This is a close-up image — 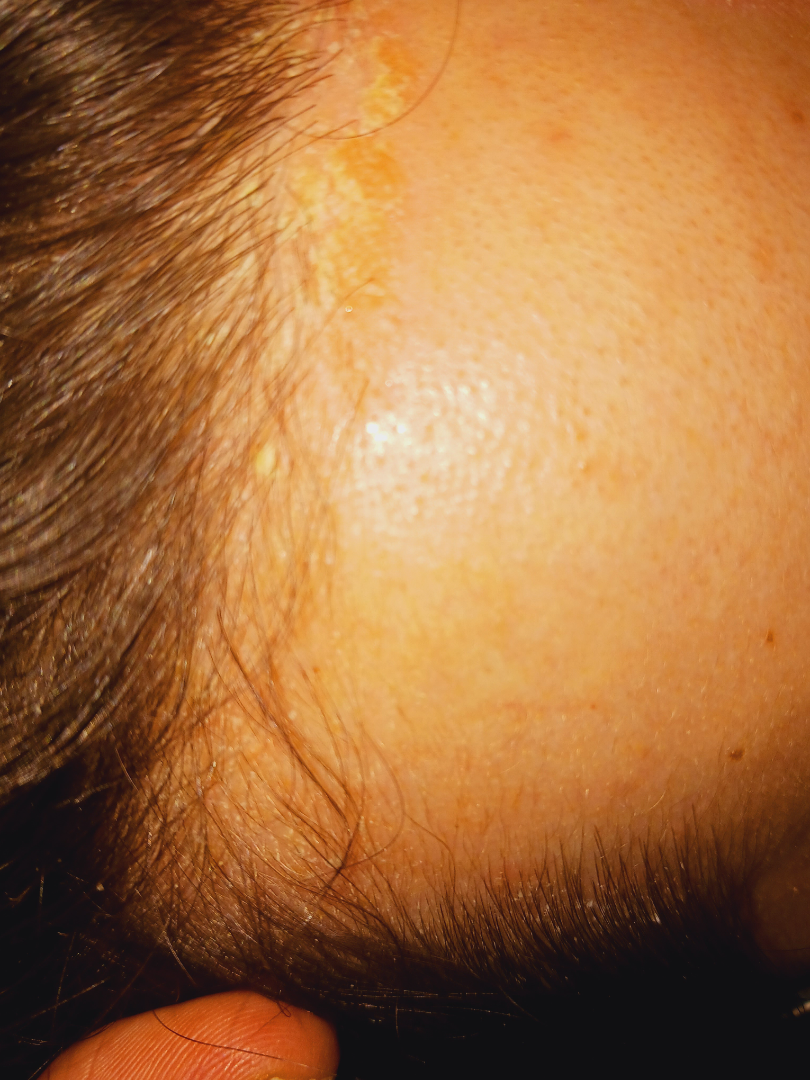clinical impression: most consistent with Seborrheic Dermatitis; with consideration of Psoriasis.